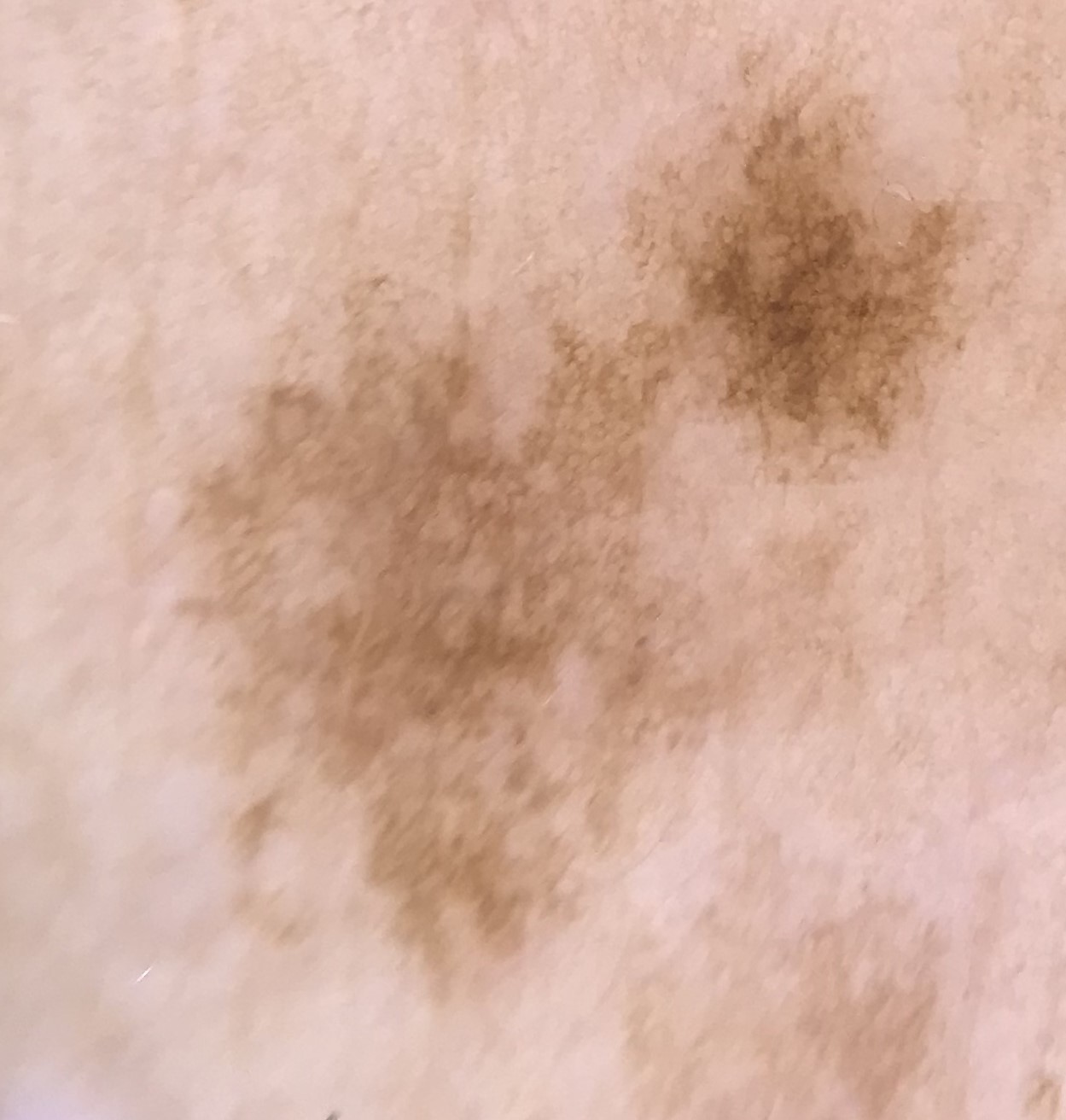The diagnosis was a benign lesion — a solar lentigo.